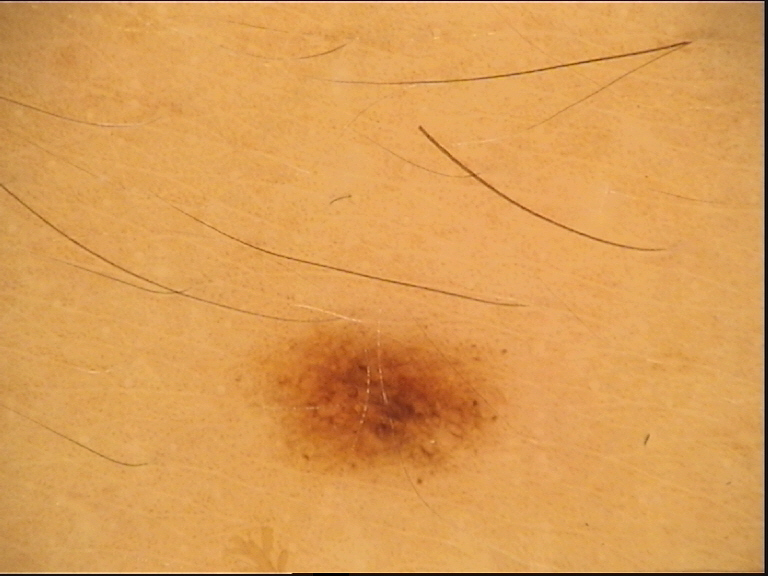Findings: A dermatoscopic image of a skin lesion. Impression: Labeled as a benign lesion — a dysplastic junctional nevus.